A clinical photograph of a skin lesion; a female subject age 78; the patient says their skin tans without first burning; acquired for a research image collection, with no referral diagnosis; by self-report, no personal history of cancer: 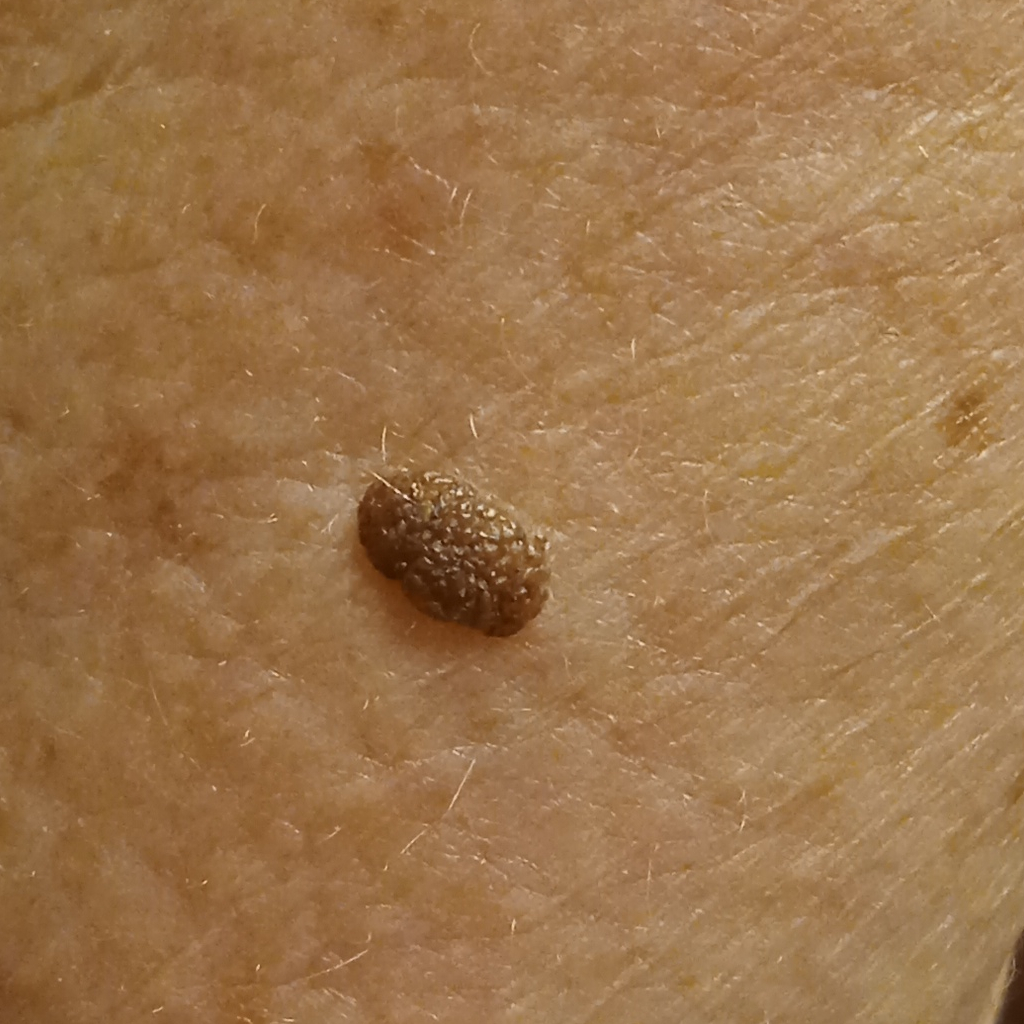- anatomic site · an arm
- lesion size · 5.6 mm
- assessment · seborrheic keratosis (dermatologist consensus)